A clinical photograph showing a skin lesion in context · a female subject aged around 65 · the patient is Fitzpatrick II.
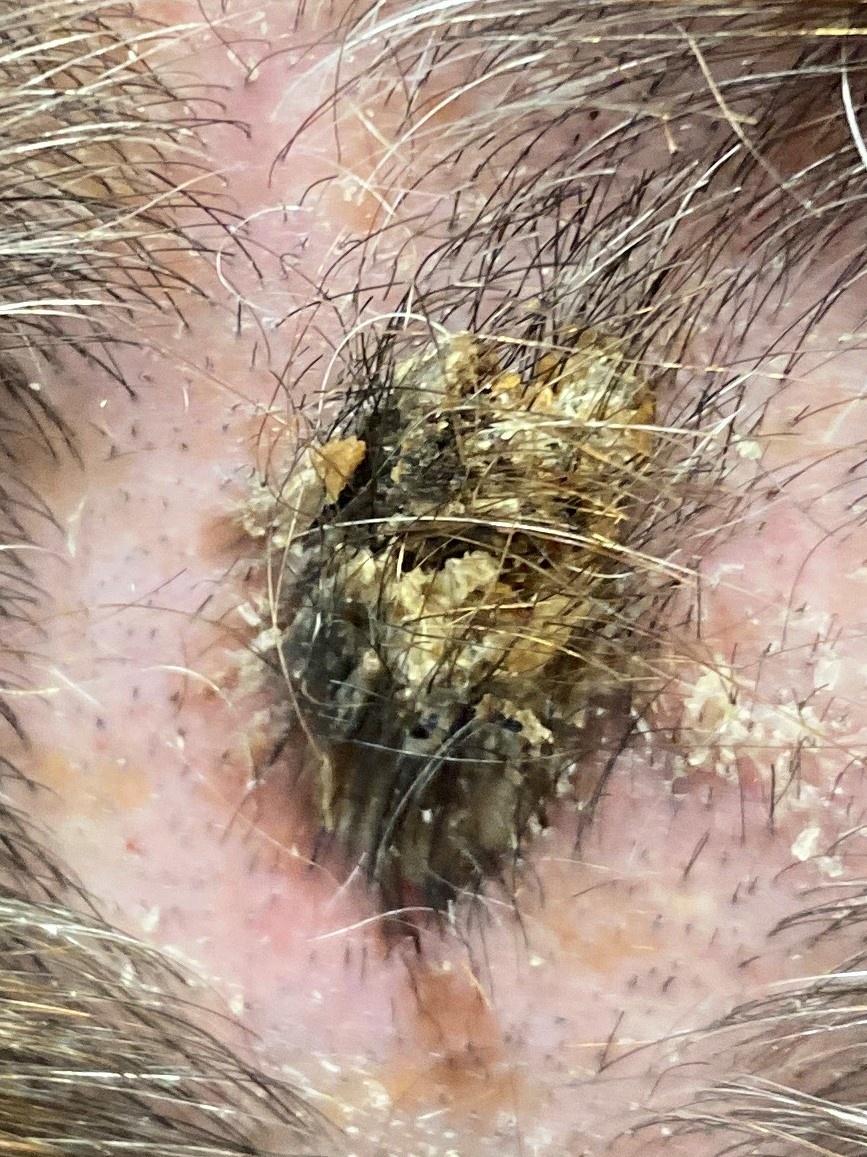The lesion involves the head or neck. Biopsy-confirmed as a malignant, adnexal lesion — a basal cell carcinoma.